The subject is a female aged 40–49; an image taken at an angle; skin tone: lay reviewers estimated 1 on the MST; reported lesion symptoms include burning, itching, pain, bleeding, bothersome appearance and enlargement; the leg is involved; the condition has been present for three to twelve months; the lesion is described as fluid-filled, raised or bumpy and rough or flaky; self-categorized by the patient as a rash: 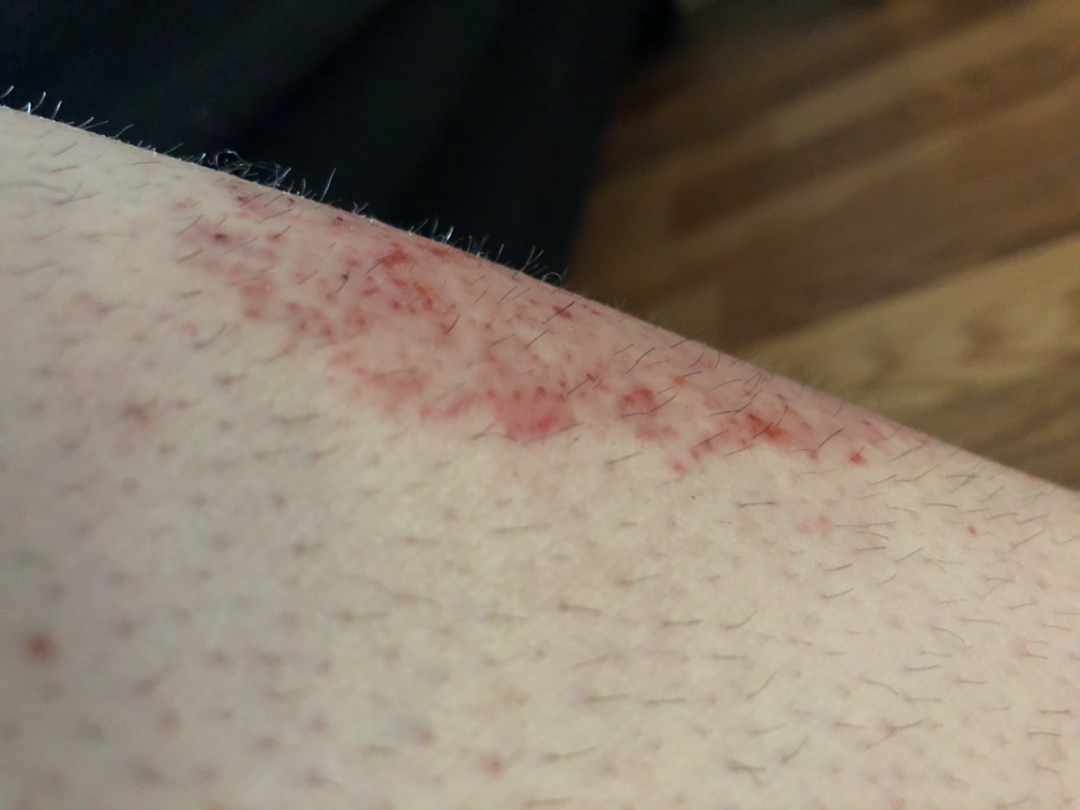clinical impression: Abrasion, scrape, or scab (54%); Tinea (23%); Eczema (23%)